A patient 45 years of age. A clinical photograph of a skin lesion.
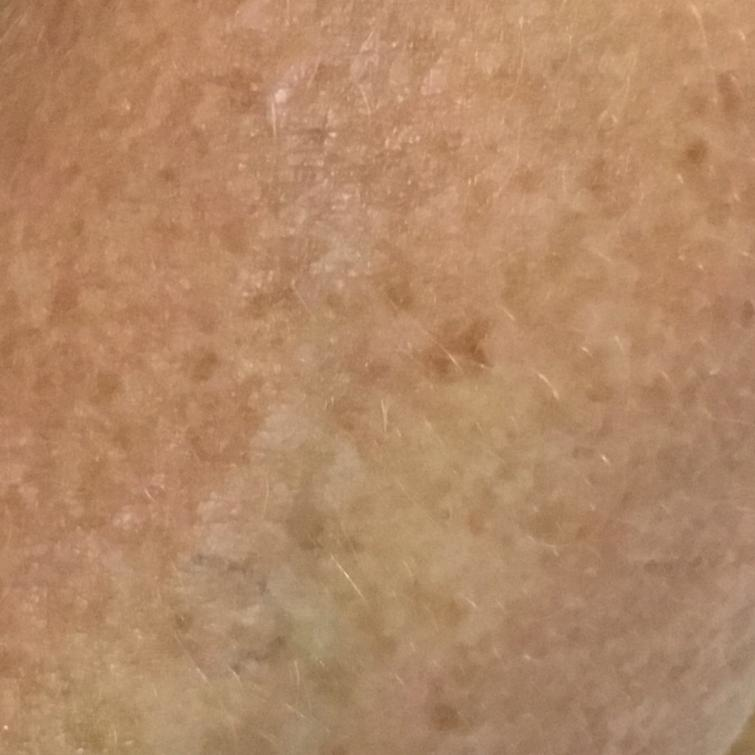lesion_location: a forearm
symptoms: none reported
diagnosis:
  name: actinic keratosis
  code: ACK
  malignancy: indeterminate
  confirmation: clinical consensus